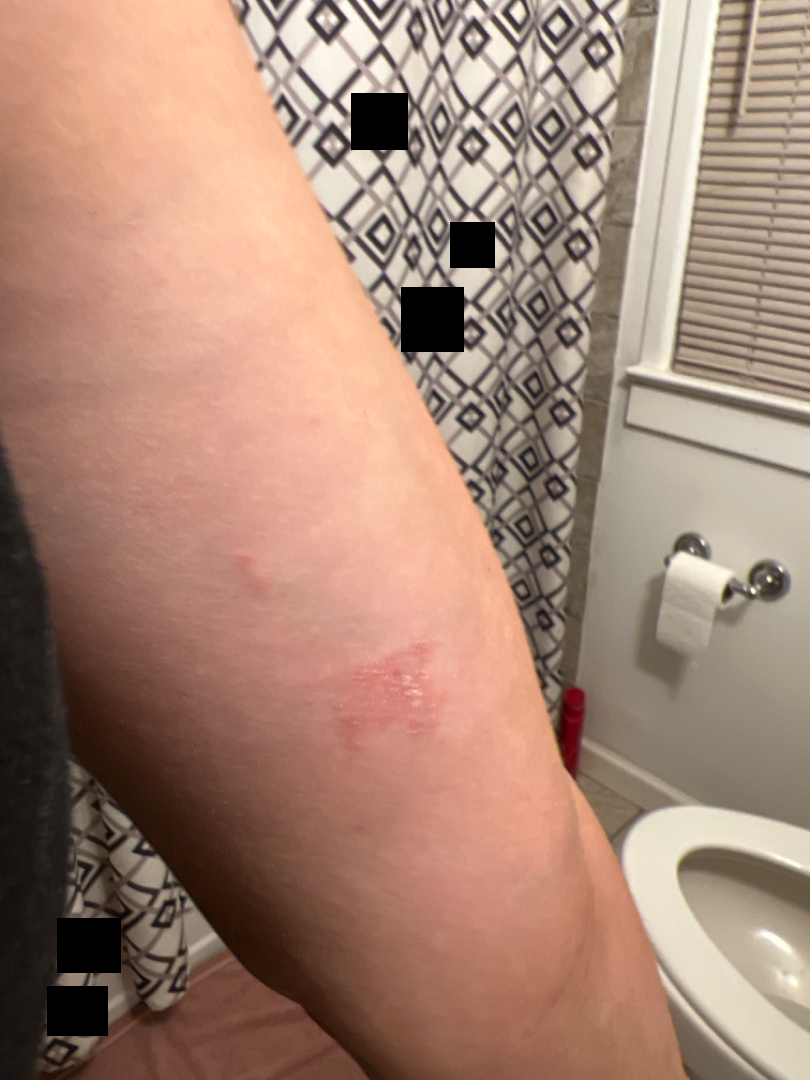subject: female, age 30–39
affected area: arm
patient's own categorization: a rash
systemic symptoms: none reported
onset: less than one week
framing: at an angle
patient-reported symptoms: itching
lesion texture: rough or flaky and raised or bumpy
dermatologist impression: the favored diagnosis is Allergic Contact Dermatitis; also raised was Psoriasis; a remote consideration is Eczema